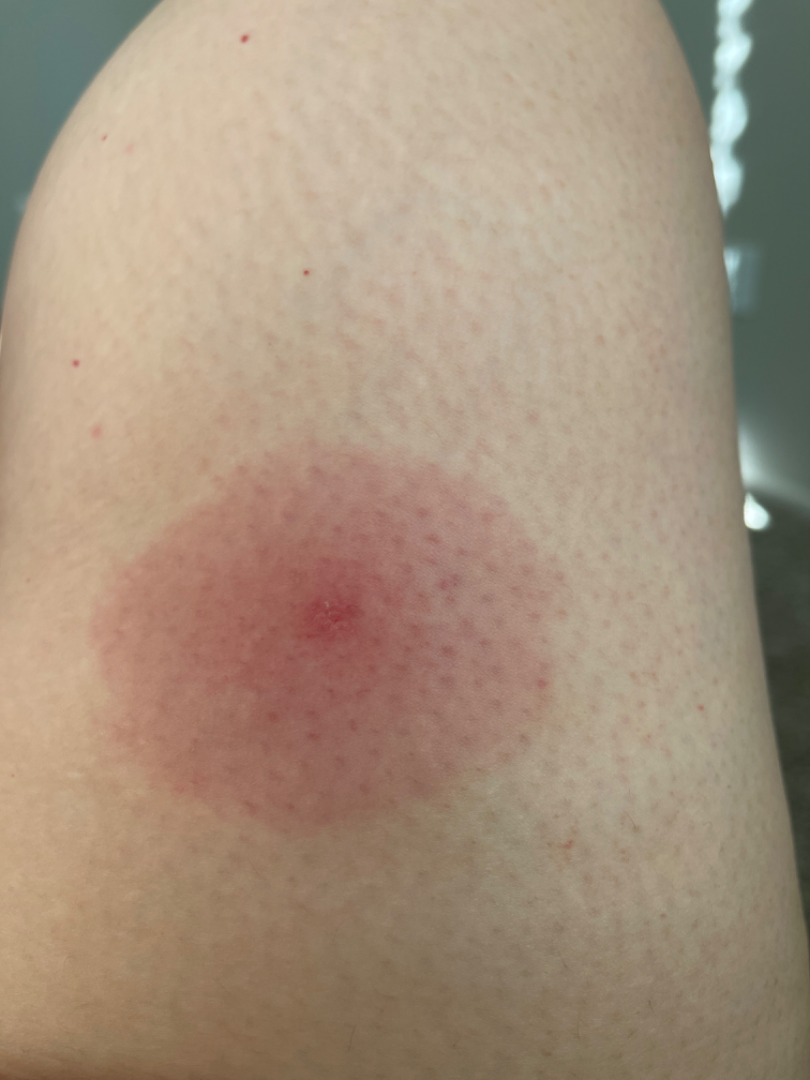Most likely Geographic tongue; possibly Insect Bite; an alternative is Drug Rash.